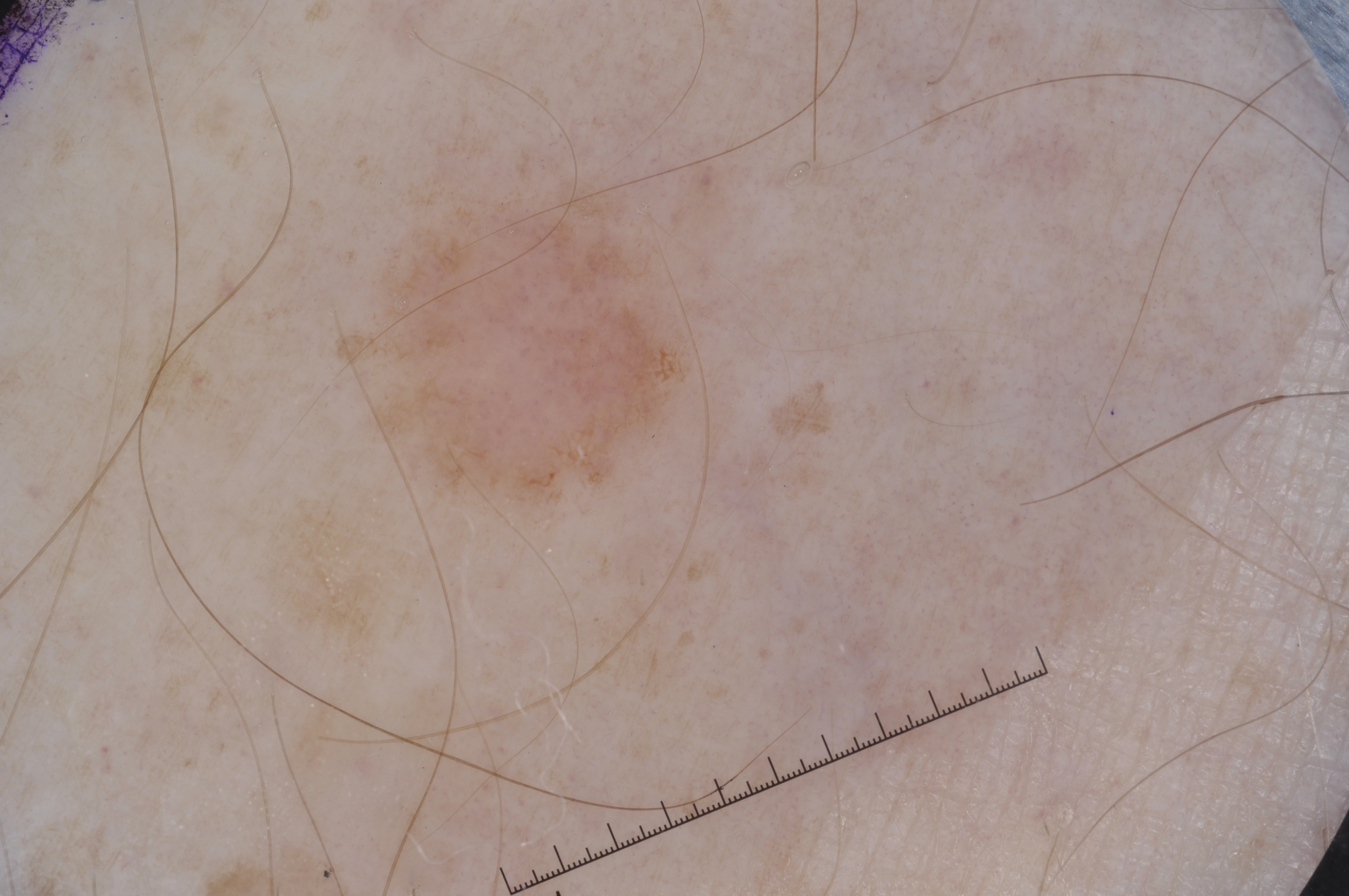Case summary: The subject is a male in their 70s. A dermatoscopic image of a skin lesion. The visible lesion spans bbox(319, 147, 703, 543). Dermoscopically, the lesion shows pigment network. A mid-sized lesion within the field. Assessment: The clinical diagnosis was a melanocytic nevus, a benign skin lesion.